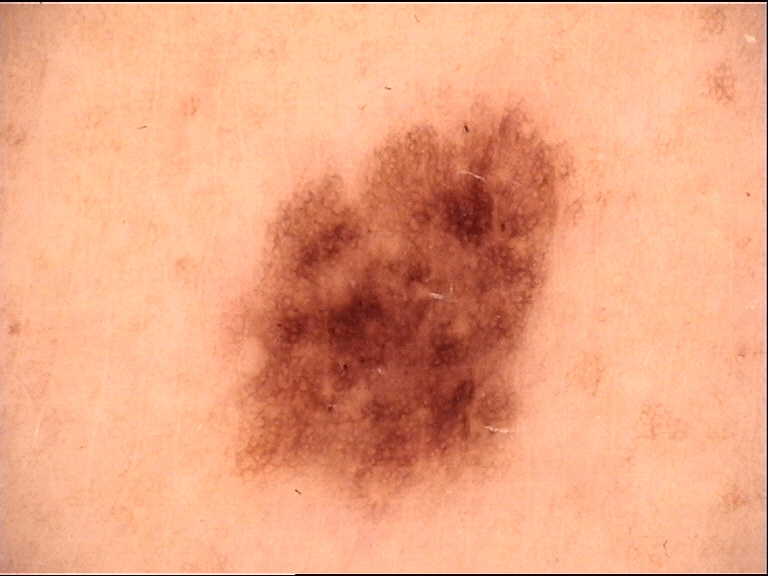A skin lesion imaged with a dermatoscope. Classified as a dysplastic junctional nevus.